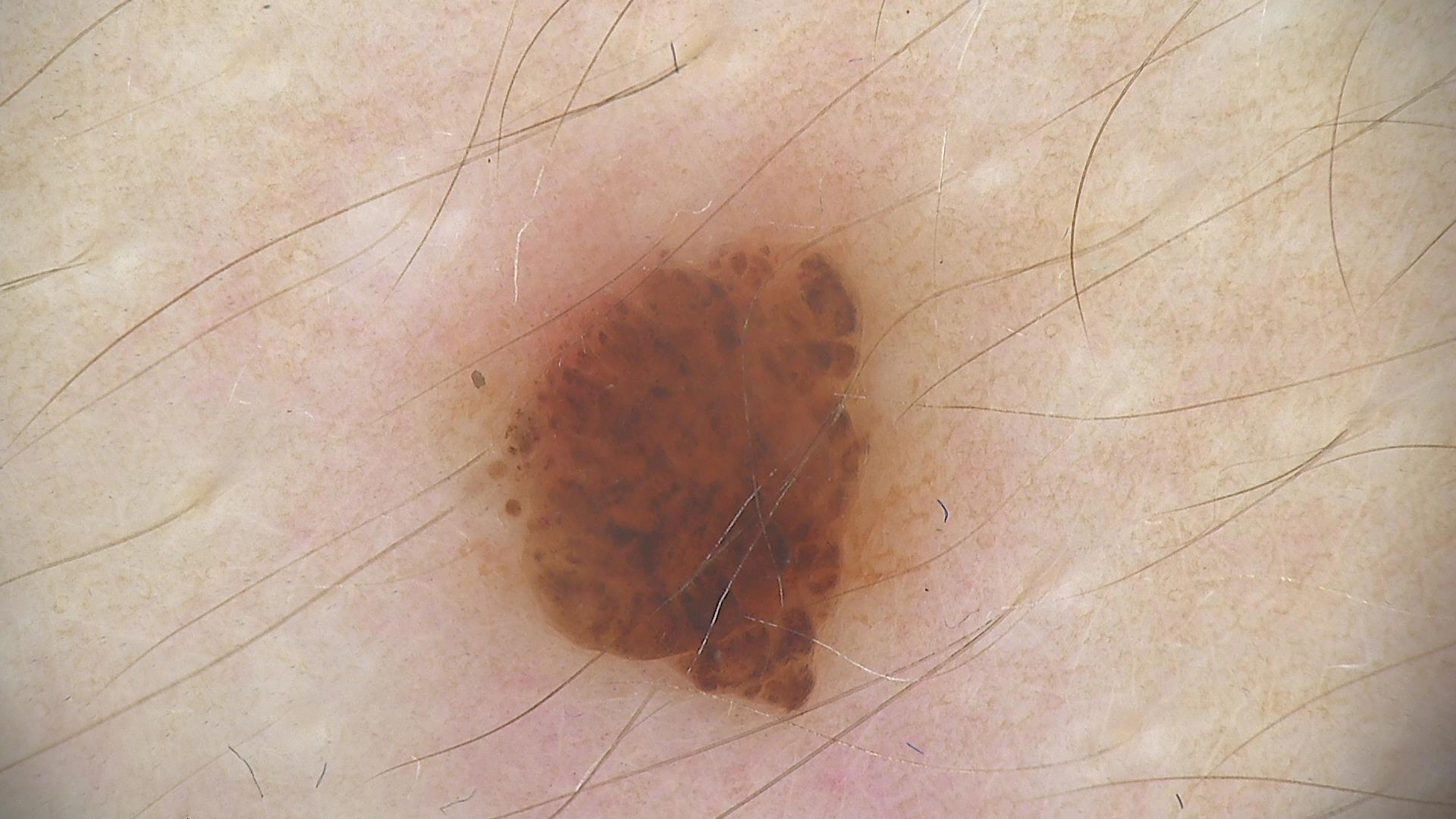Case: The morphology is that of a banal lesion. Conclusion: Labeled as a compound nevus.